A skin lesion imaged with a dermatoscope:
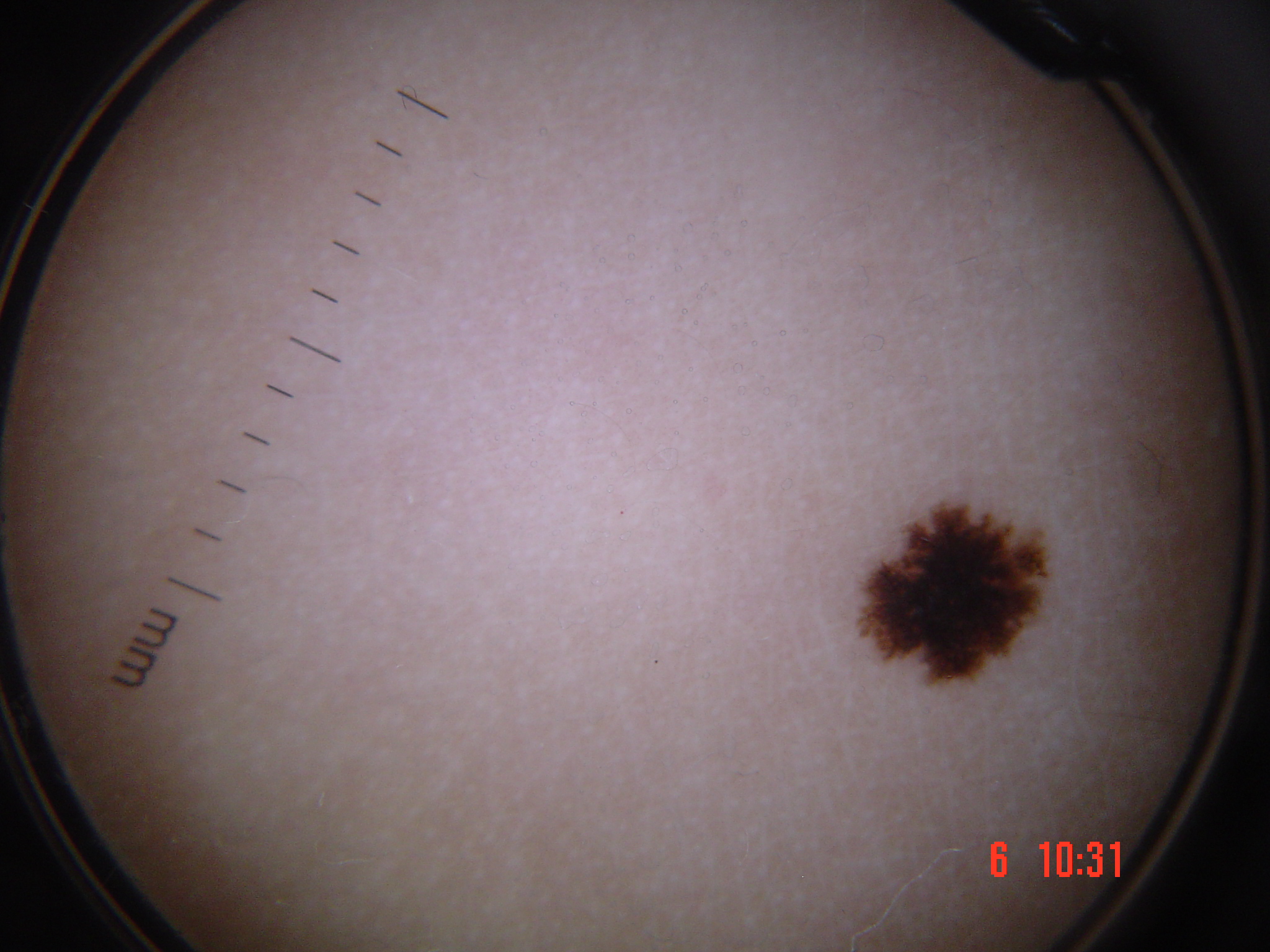Case:
– diagnostic label · dysplastic junctional nevus (expert consensus)